The patient reports the condition has been present for one to three months · the subject is a female aged 60–69 · located on the leg · associated systemic symptoms include joint pain, shortness of breath and fatigue · the lesion is associated with burning, enlargement, pain and bothersome appearance · the lesion is described as raised or bumpy, rough or flaky, fluid-filled and flat · a close-up photograph · the patient considered this a rash · non-clinician graders estimated MST 1 or 2.
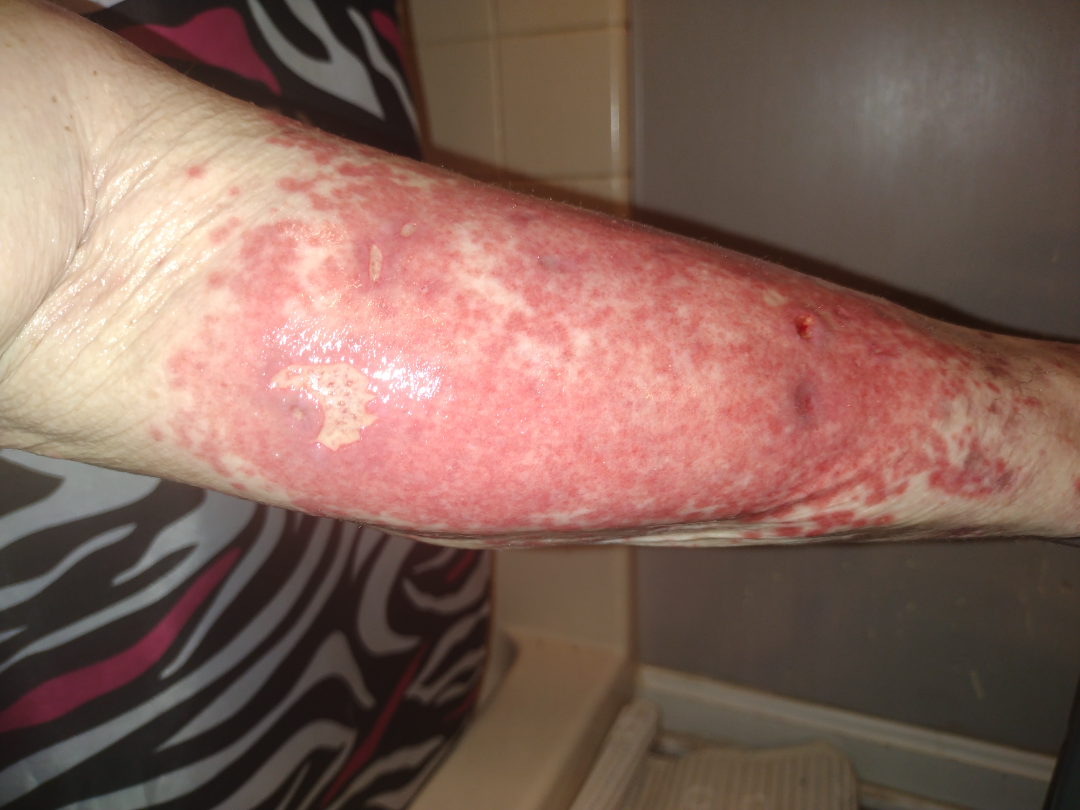Findings:
Reviewed remotely by three dermatologists: Leukocytoclastic Vasculitis and Cellulitis were considered with similar weight; possibly Impetigo.